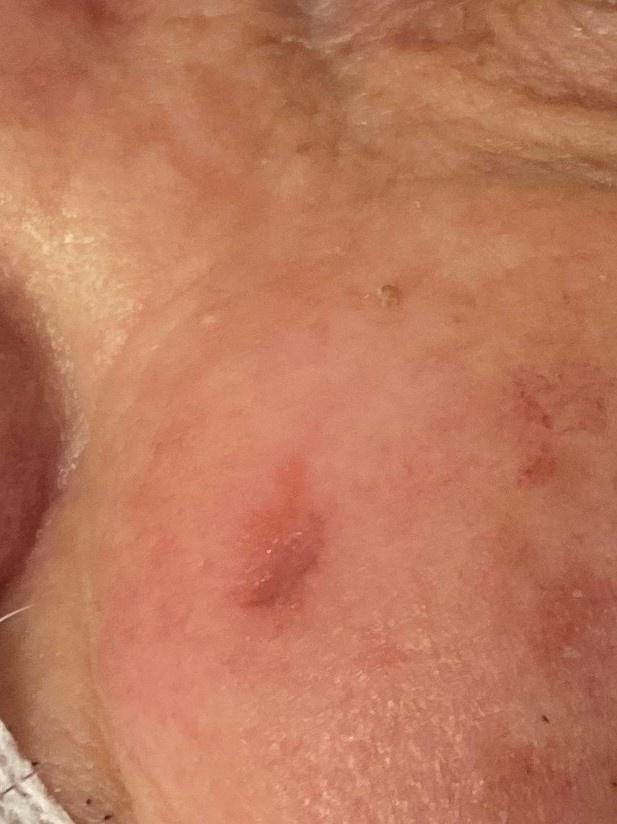Findings:
The patient is Fitzpatrick phototype II. A clinical photograph showing a skin lesion in context. The lesion is located on the head or neck.
Diagnosis:
Histopathology confirmed an epidermal lesion — a squamous cell carcinoma.